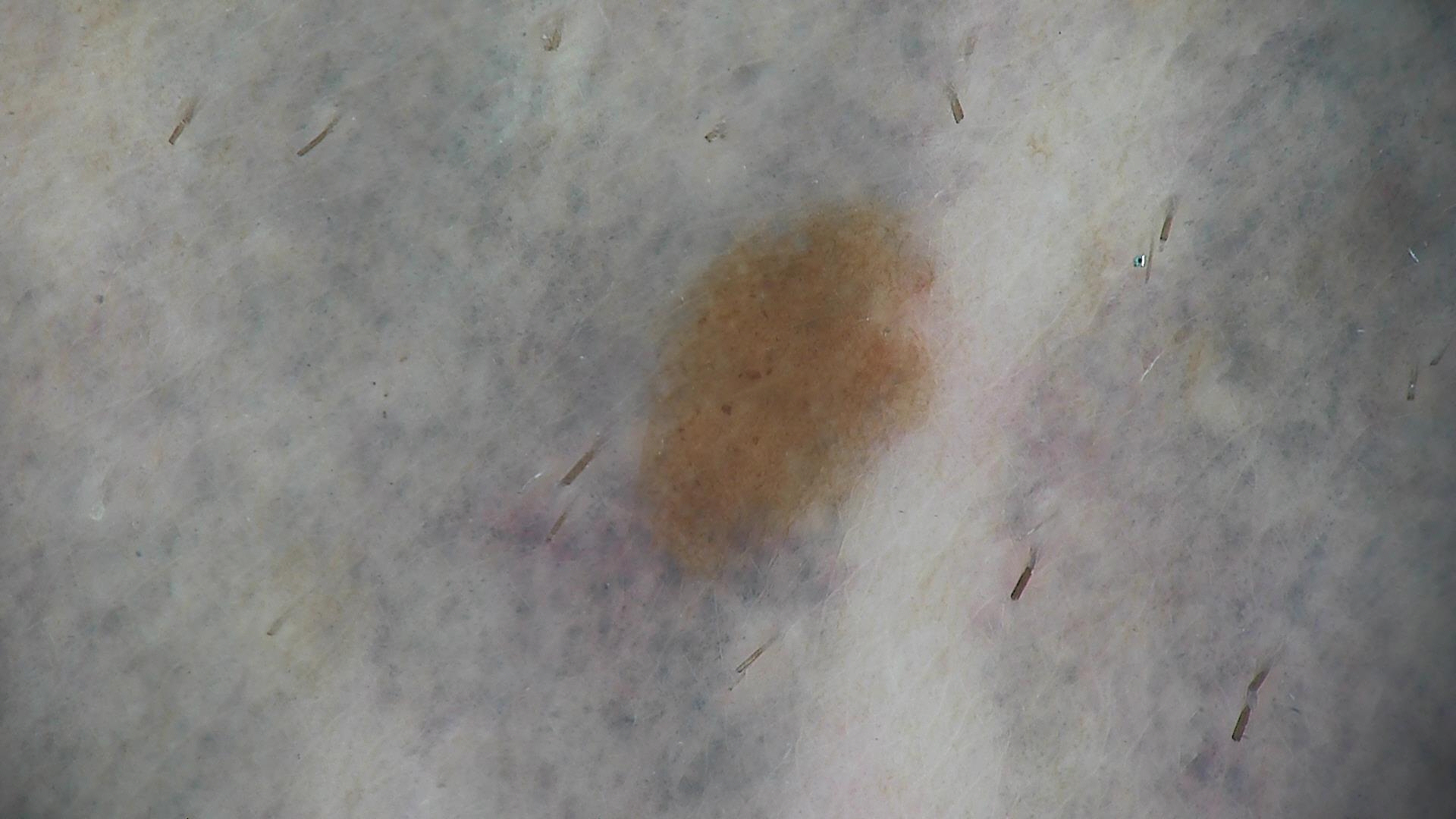Labeled as a benign lesion — a dysplastic junctional nevus.